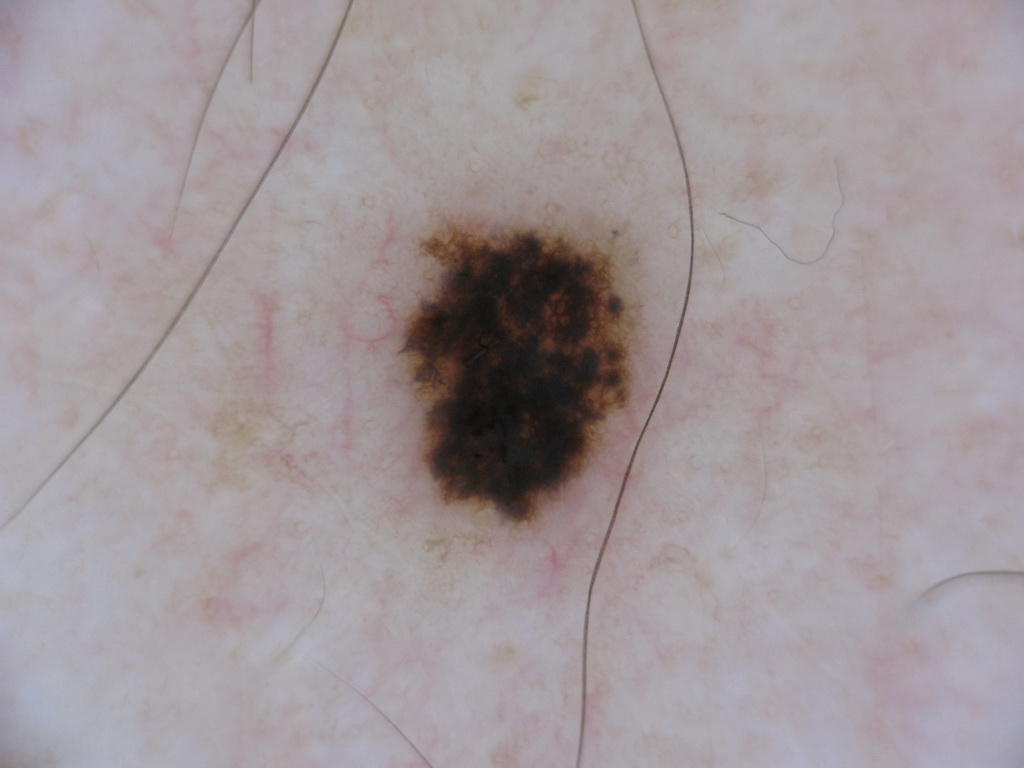A dermoscopic image of a skin lesion. As (left, top, right, bottom), the lesion spans <bbox>395, 218, 638, 526</bbox>. Dermoscopic examination shows pigment network, with no streaks, globules, milia-like cysts, or negative network. Expert review diagnosed this as a melanocytic nevus, a benign lesion.